The photo was captured at an angle; the arm is involved.
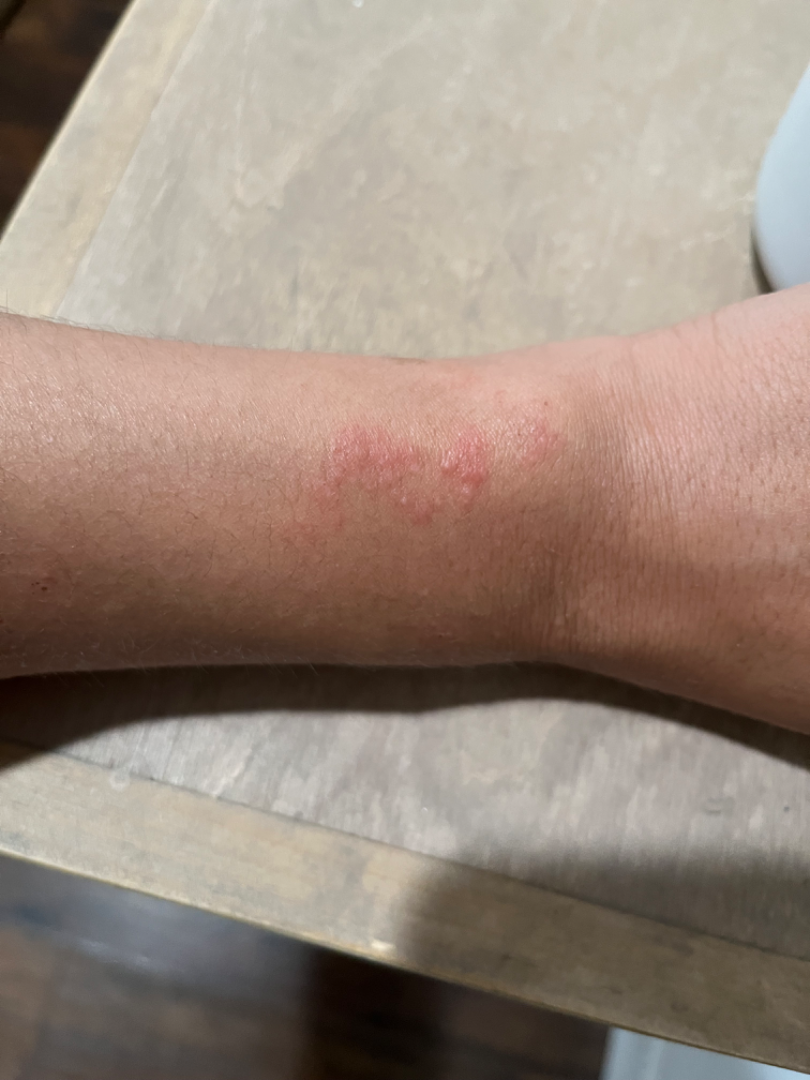Notes:
• clinical impression: Allergic Contact Dermatitis (primary); Irritant Contact Dermatitis (possible)